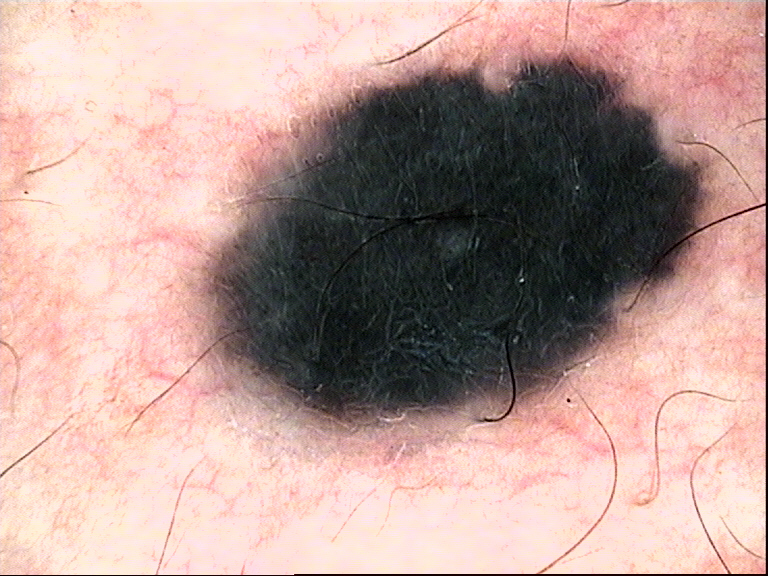<lesion>
  <diagnosis>
    <name>blue nevus</name>
    <code>bdb</code>
    <malignancy>benign</malignancy>
    <super_class>melanocytic</super_class>
    <confirmation>expert consensus</confirmation>
  </diagnosis>
</lesion>